The lesion involves the head or neck, arm and leg; this image was taken at an angle.
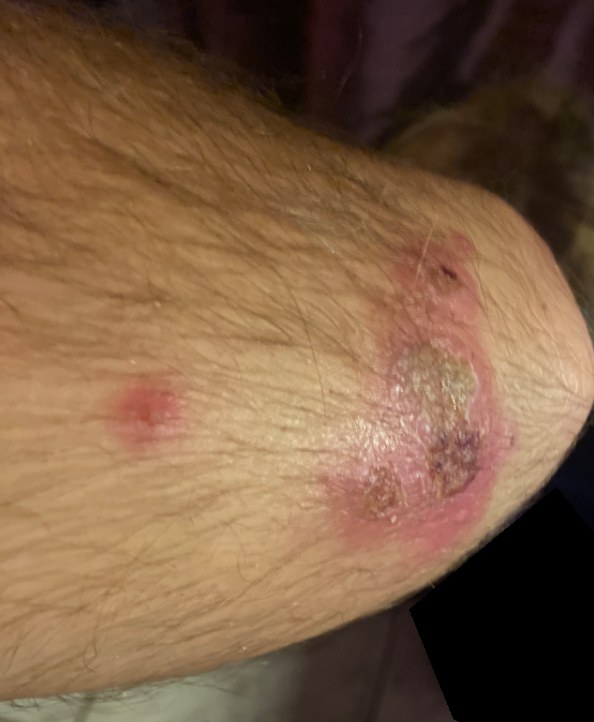* assessment — not assessable